The patient is a female aged 50–59; located on the arm; the photograph was taken at a distance — 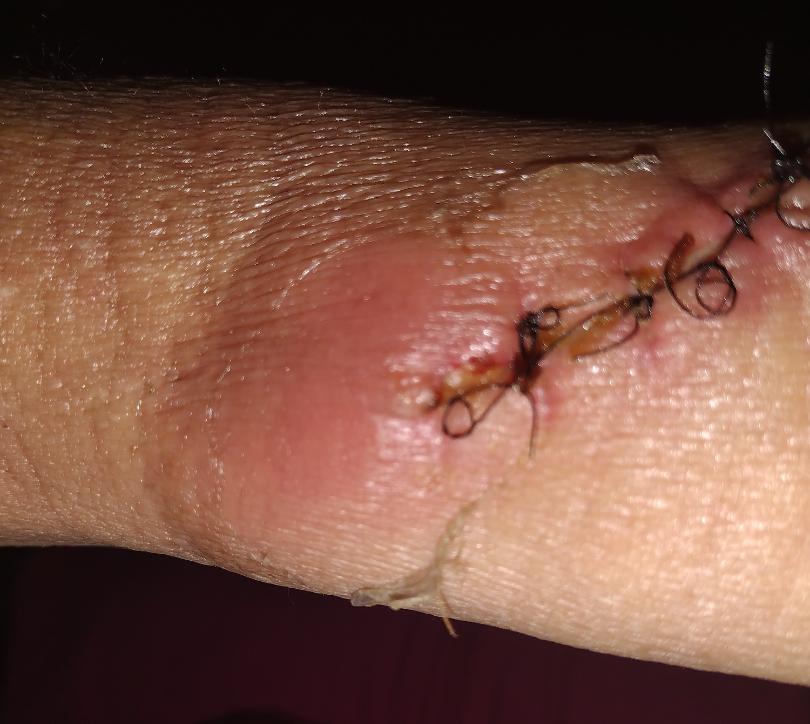Notes:
* described texture · fluid-filled
* symptoms · darkening, burning, enlargement, itching, bleeding, bothersome appearance and pain
* diagnostic considerations · Inflicted skin lesions (weight 0.50); Skin ulcer (weight 0.29); Dehiscence (weight 0.21)